An image taken at an angle. The patient is a female aged 40–49. The lesion involves the arm — 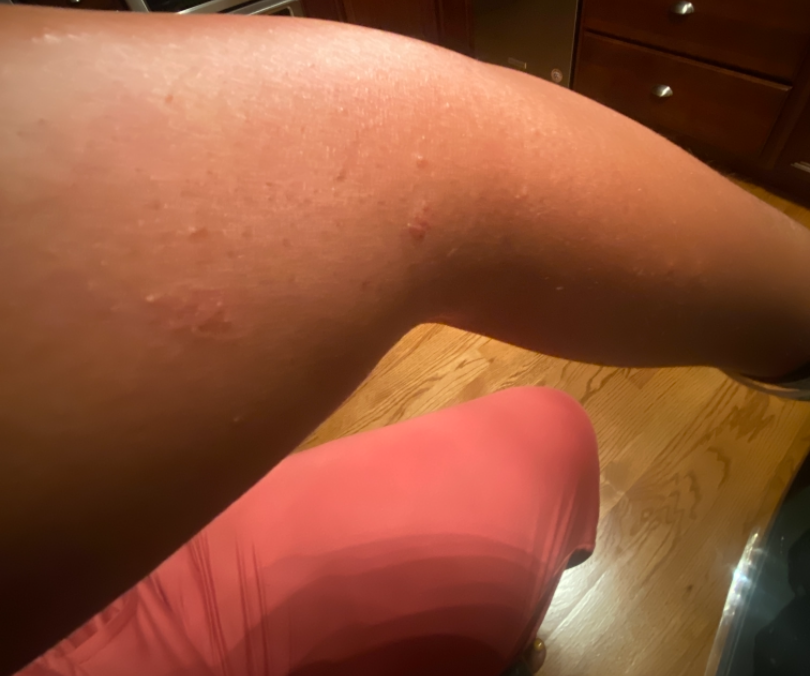Findings:
The case was indeterminate on photographic review.